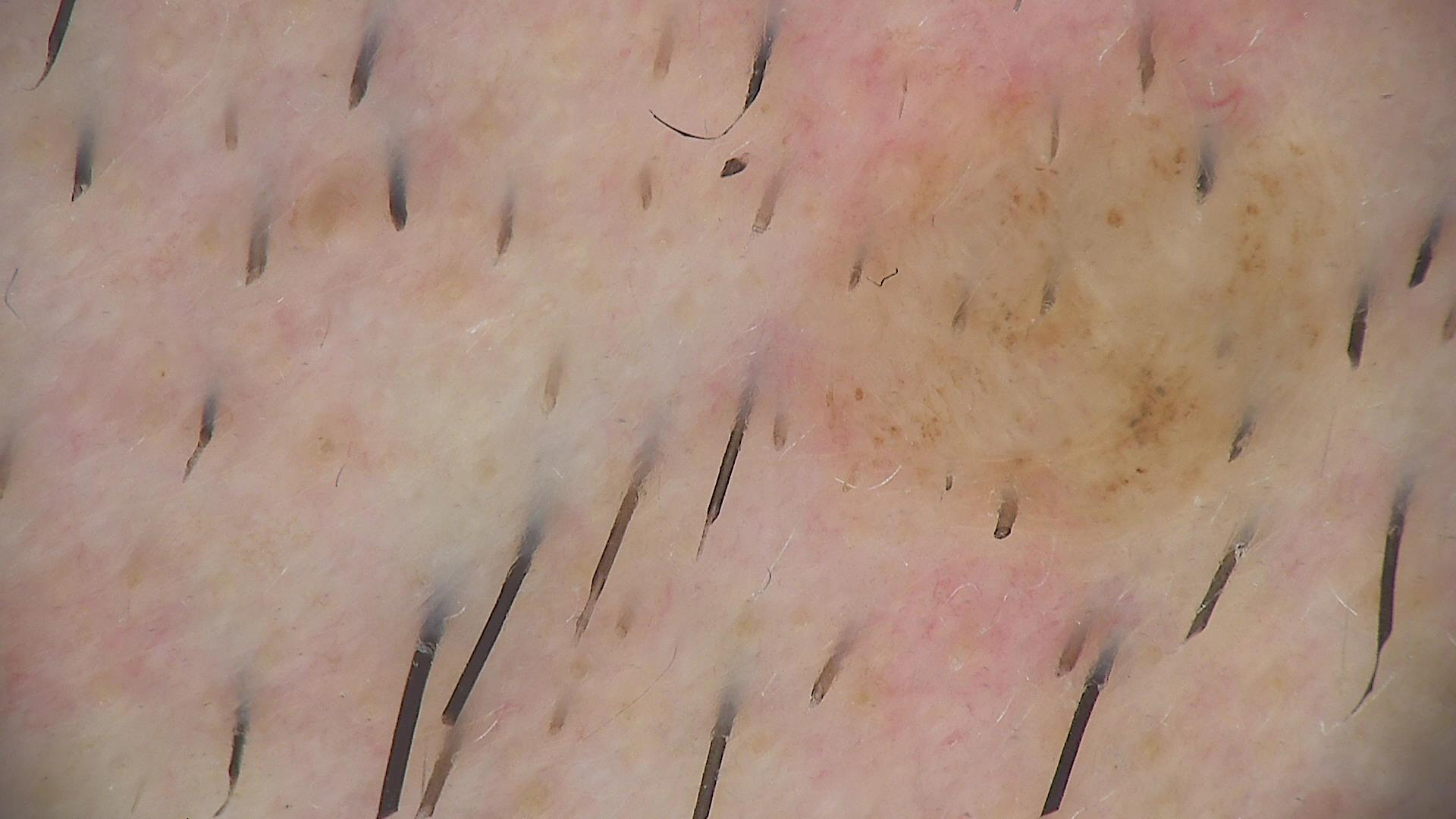diagnostic label: dermal nevus (expert consensus).